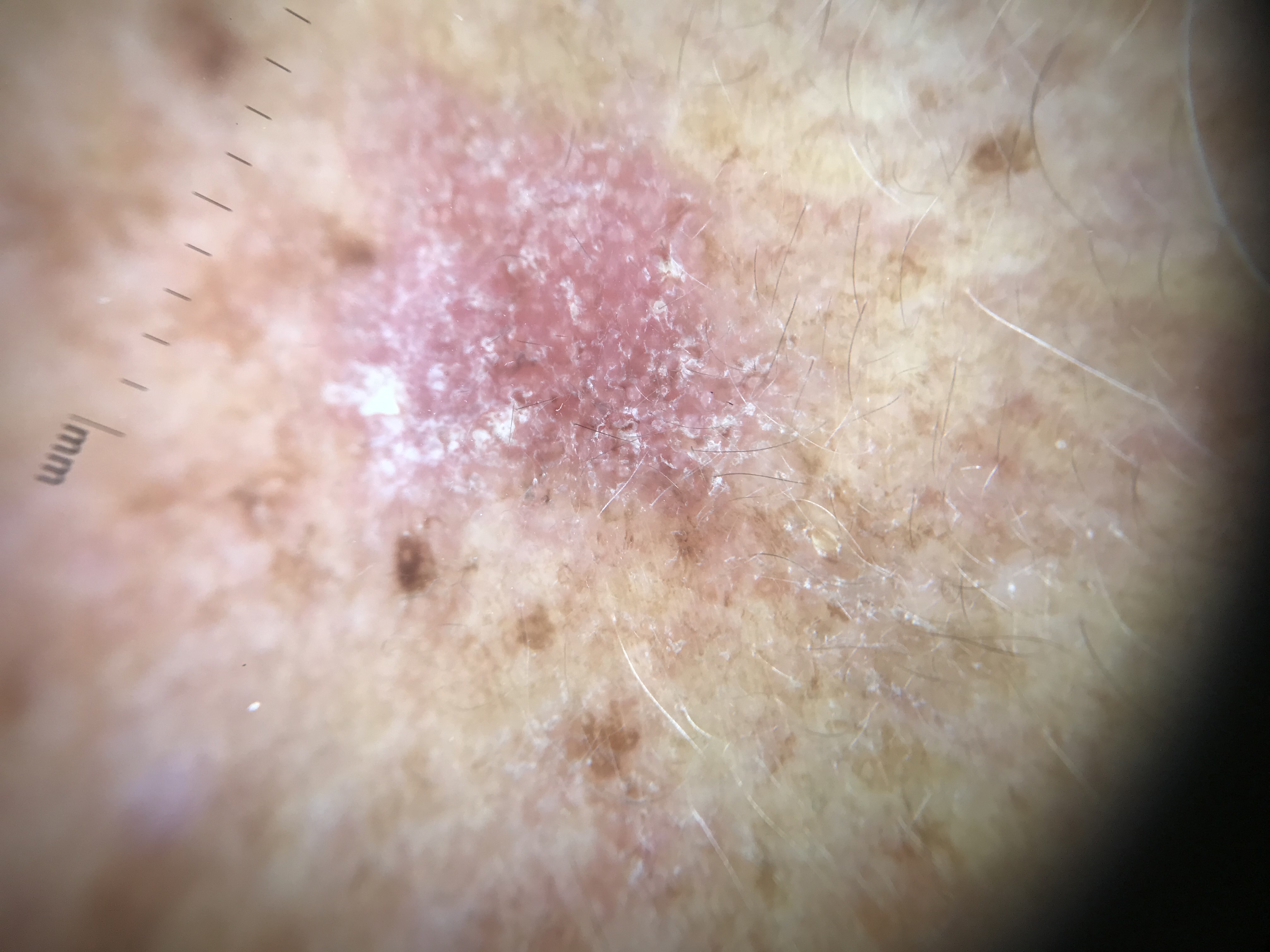The diagnosis was an actinic keratosis.